The head or neck is involved · the contributor is male · the photograph was taken at an angle — 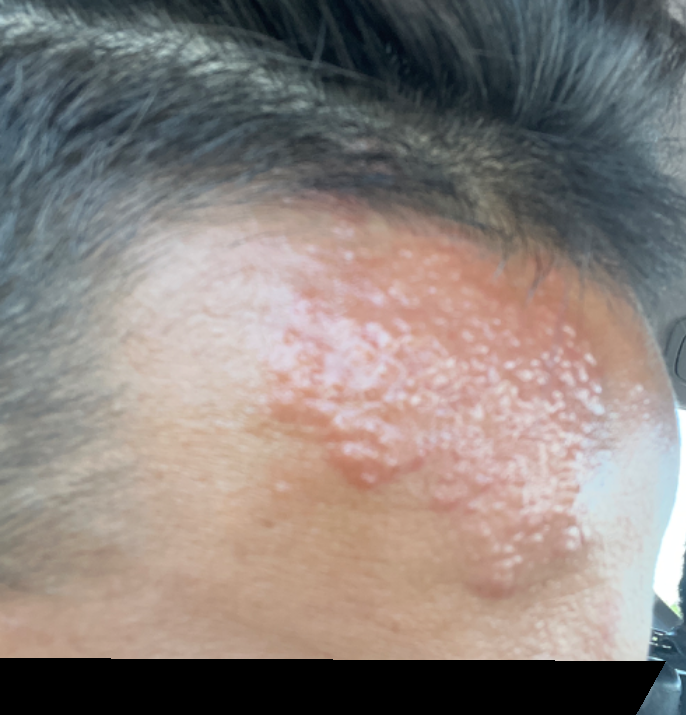<dermatology_case>
  <symptoms>none reported</symptoms>
  <duration>about one day</duration>
  <patient_category>a rash</patient_category>
  <texture>fluid-filled, raised or bumpy</texture>
  <skin_tone>
    <fitzpatrick>IV</fitzpatrick>
    <monk_skin_tone>4, 6</monk_skin_tone>
  </skin_tone>
  <differential>
    <tied_lead>Impetigo, Granuloma faciale, Herpes Simplex, Crohn disease of skin, Localised skin infection, Granulomatous disorder of the skin and subcutaneous tissue</tied_lead>
  </differential>
</dermatology_case>